Located on the leg · this is a close-up image:
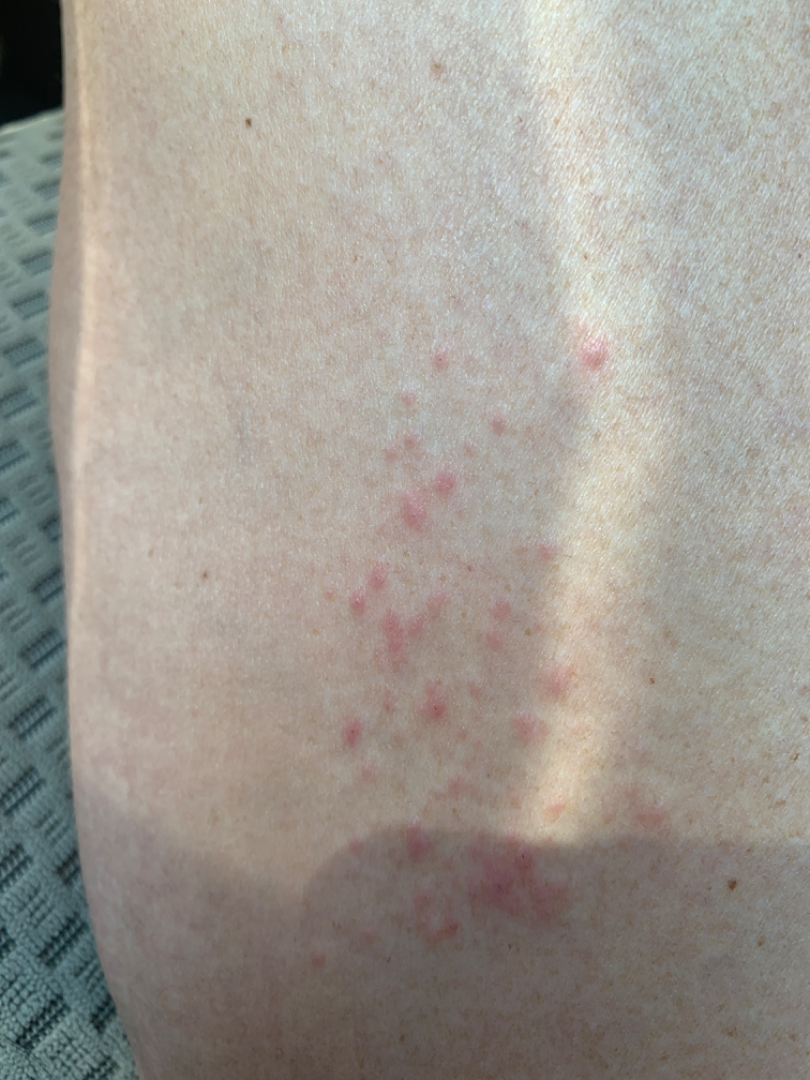Impression: On photographic review by a dermatologist, the impression was split between Folliculitis and Irritant Contact Dermatitis.